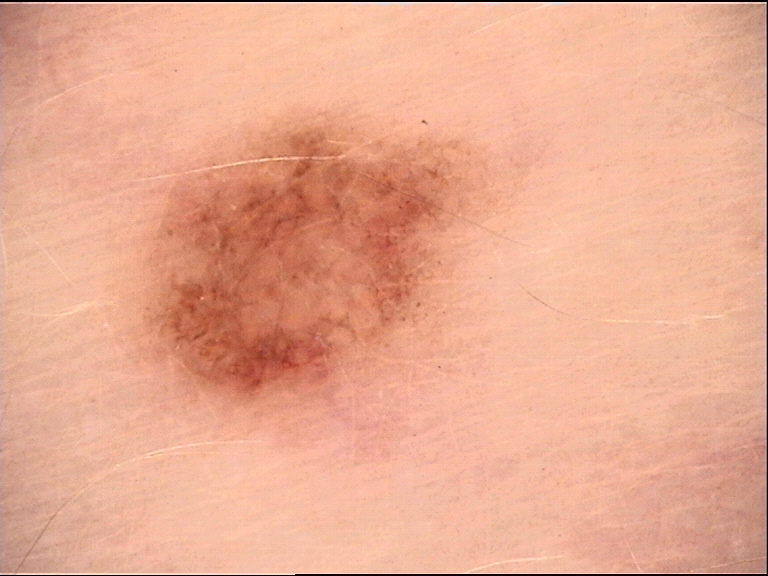Summary: Dermoscopy of a skin lesion. This is a banal lesion. Impression: Classified as a compound nevus.